FST II · a wide-field clinical photograph of a skin lesion · a male subject in their mid- to late 80s or older:
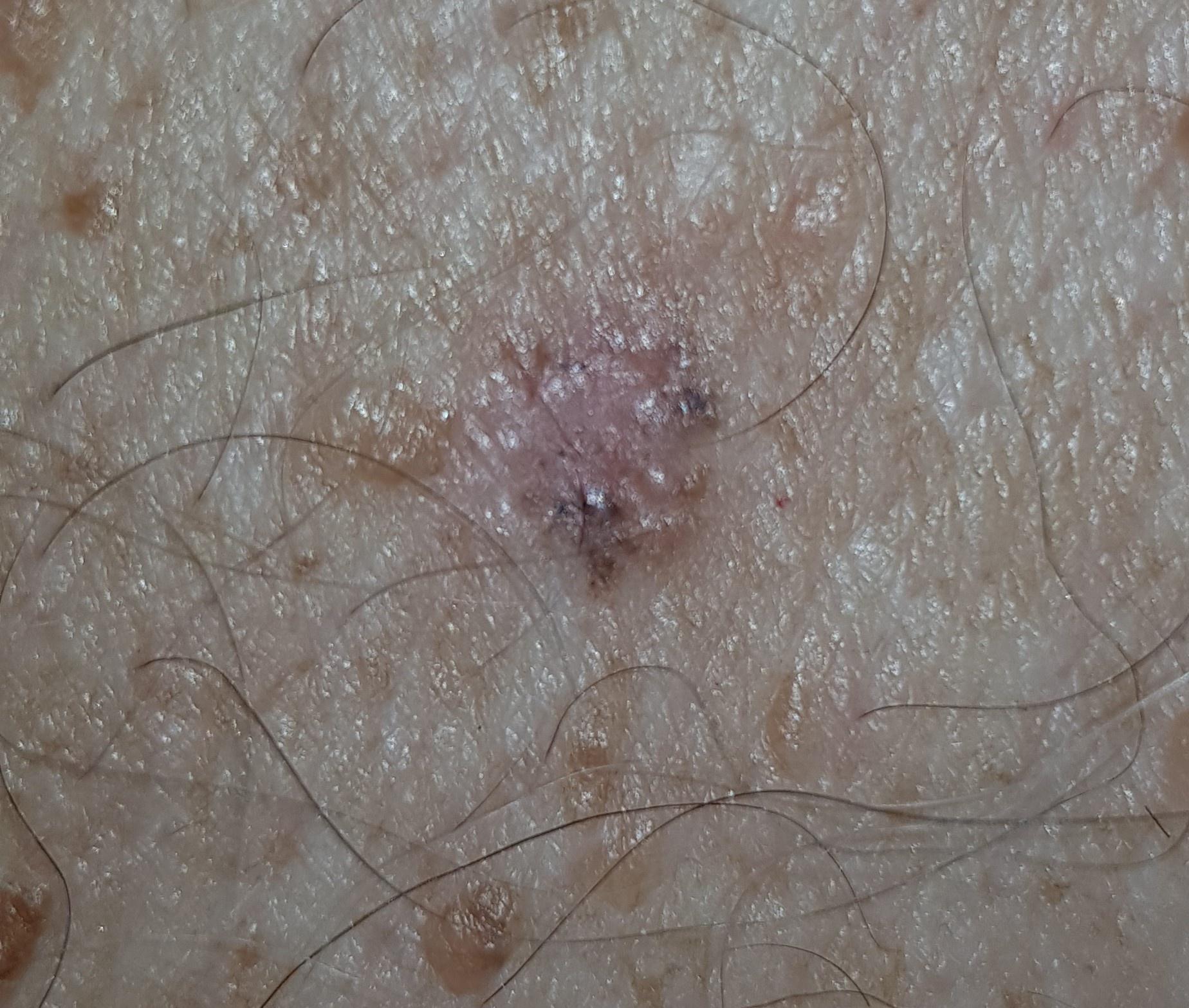{"lesion_location": {"region": "the trunk"}, "diagnosis": {"name": "Basal cell carcinoma", "malignancy": "malignant", "confirmation": "histopathology", "lineage": "adnexal"}}